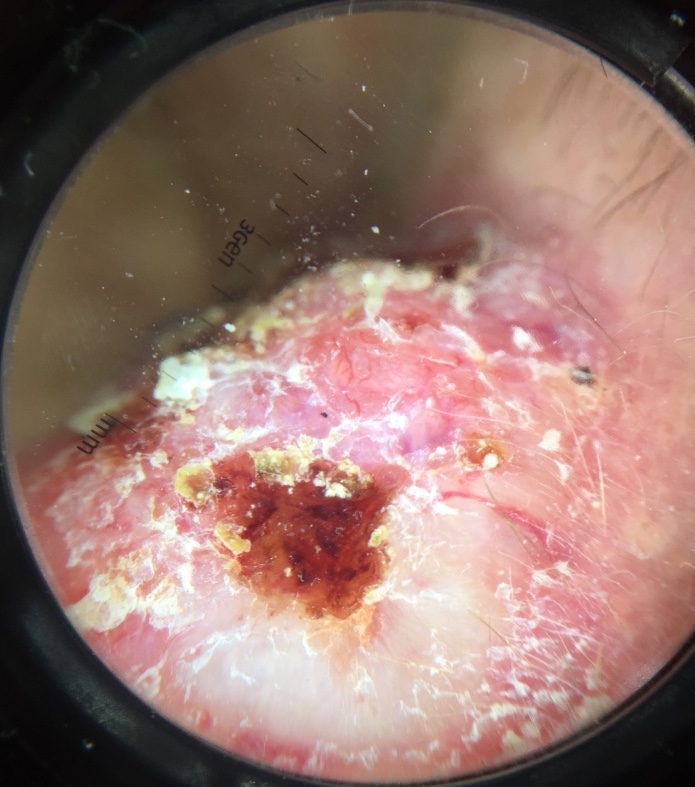Pathology:
The biopsy diagnosis was a skin cancer — a basal cell carcinoma.